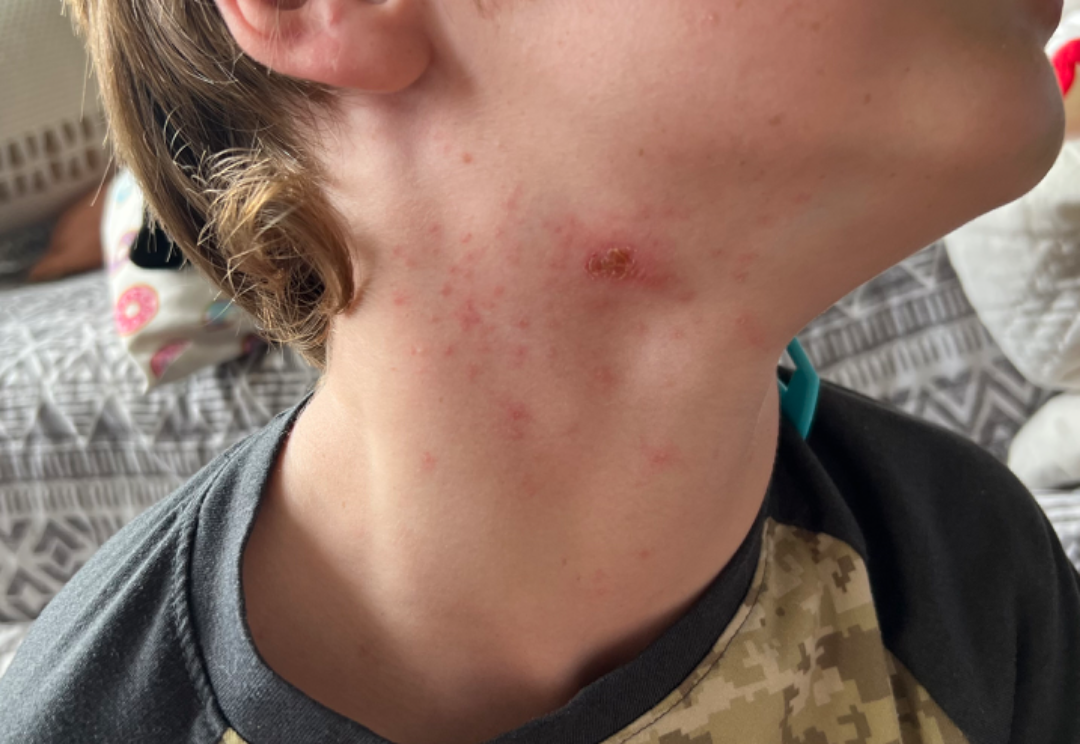FST I. The photograph is a close-up of the affected area. The reviewing dermatologist's impression was: Impetigo and Allergic Contact Dermatitis were each considered, in no particular order.